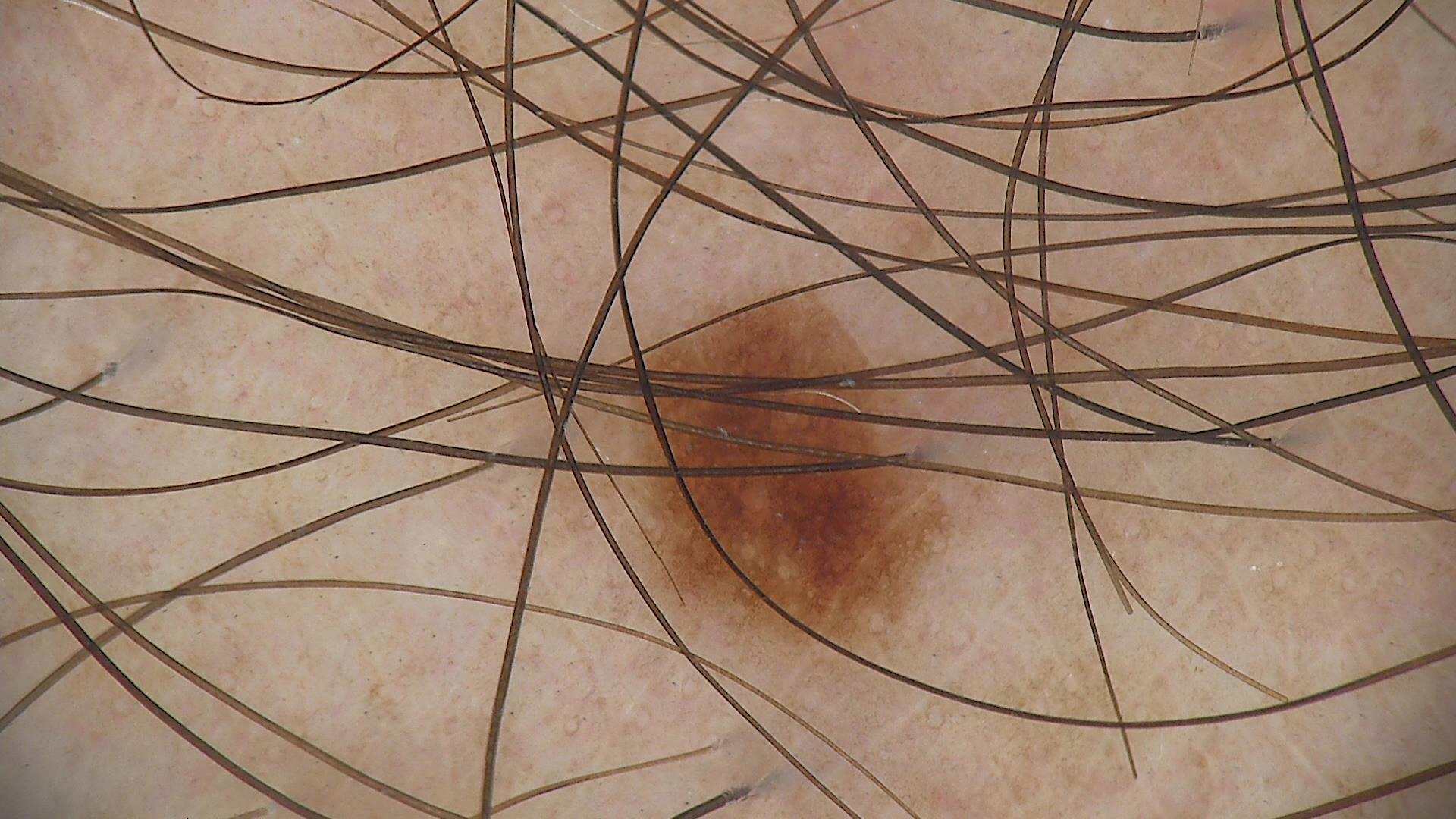Consistent with a dysplastic junctional nevus.